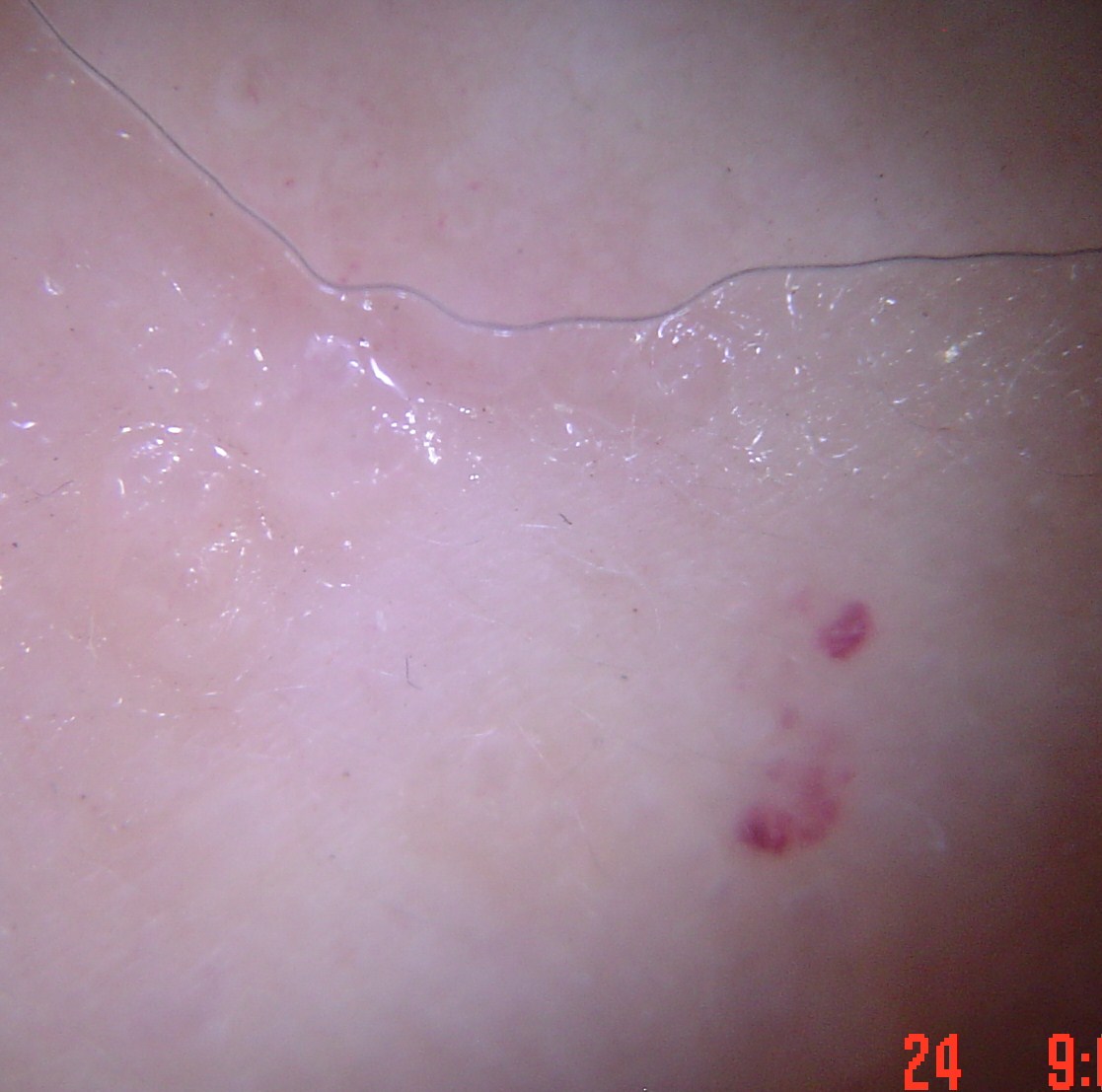diagnosis:
  name: hemangioma
  code: ha
  malignancy: benign
  super_class: non-melanocytic
  confirmation: expert consensus